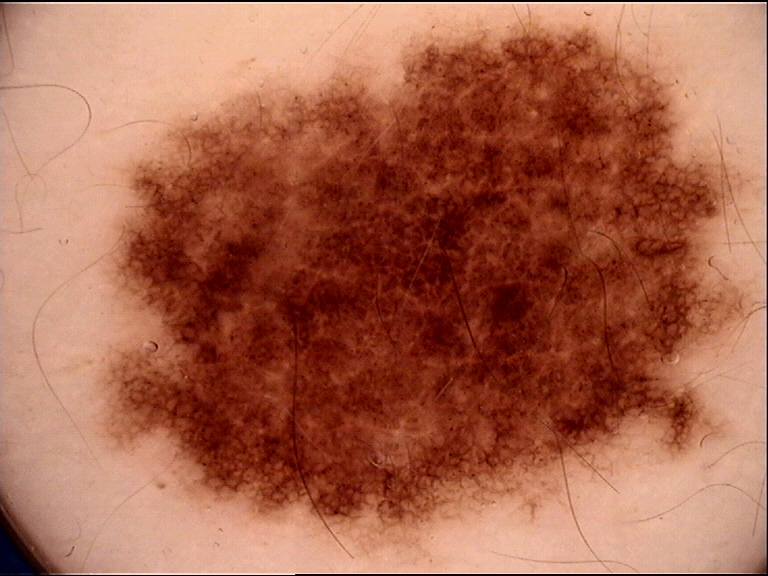Conclusion: Classified as a dysplastic junctional nevus.